A dermoscopic image of a skin lesion.
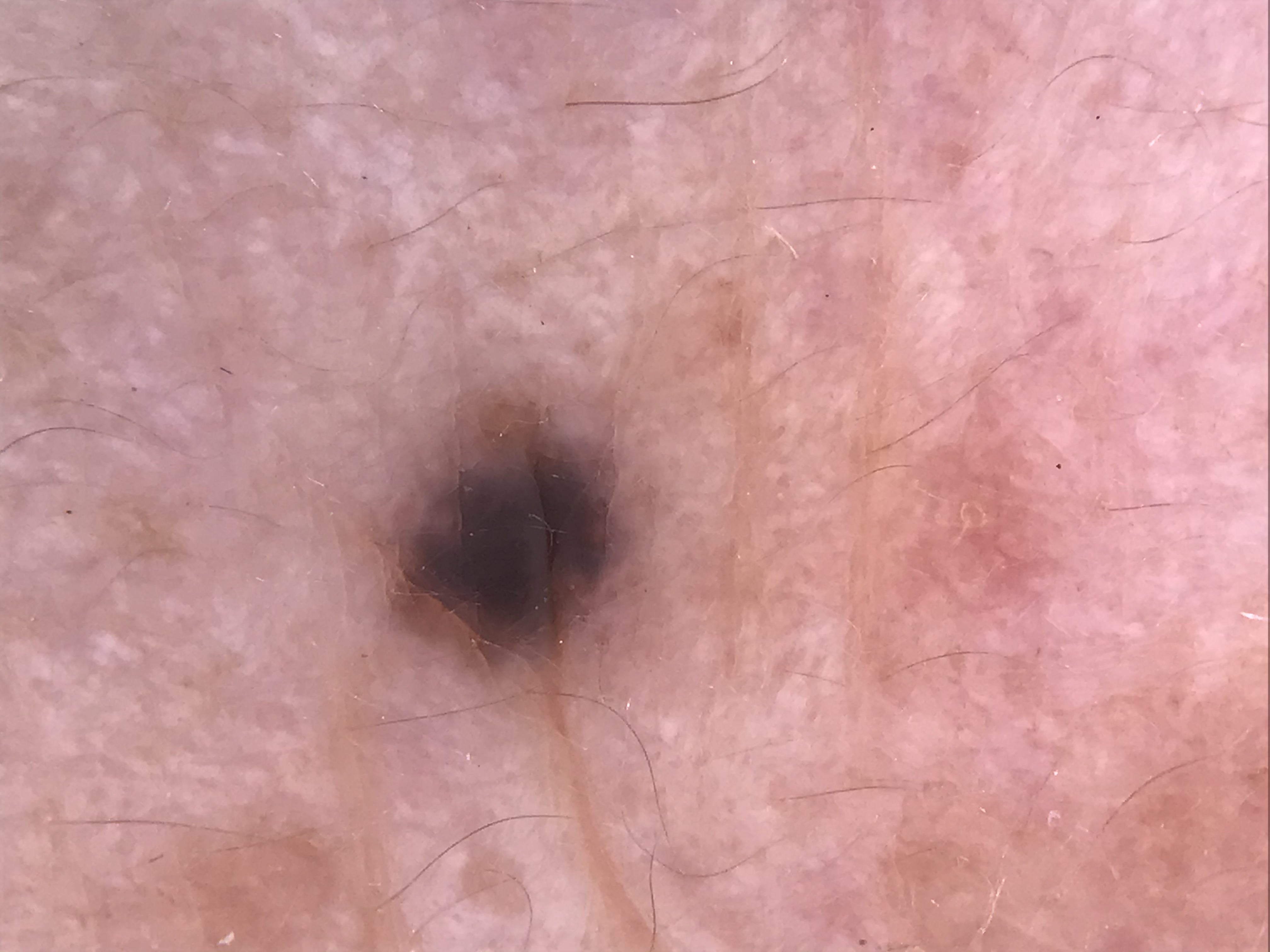The architecture is that of a dermal, banal lesion. Consistent with a blue nevus.